Dermoscopy of a skin lesion.
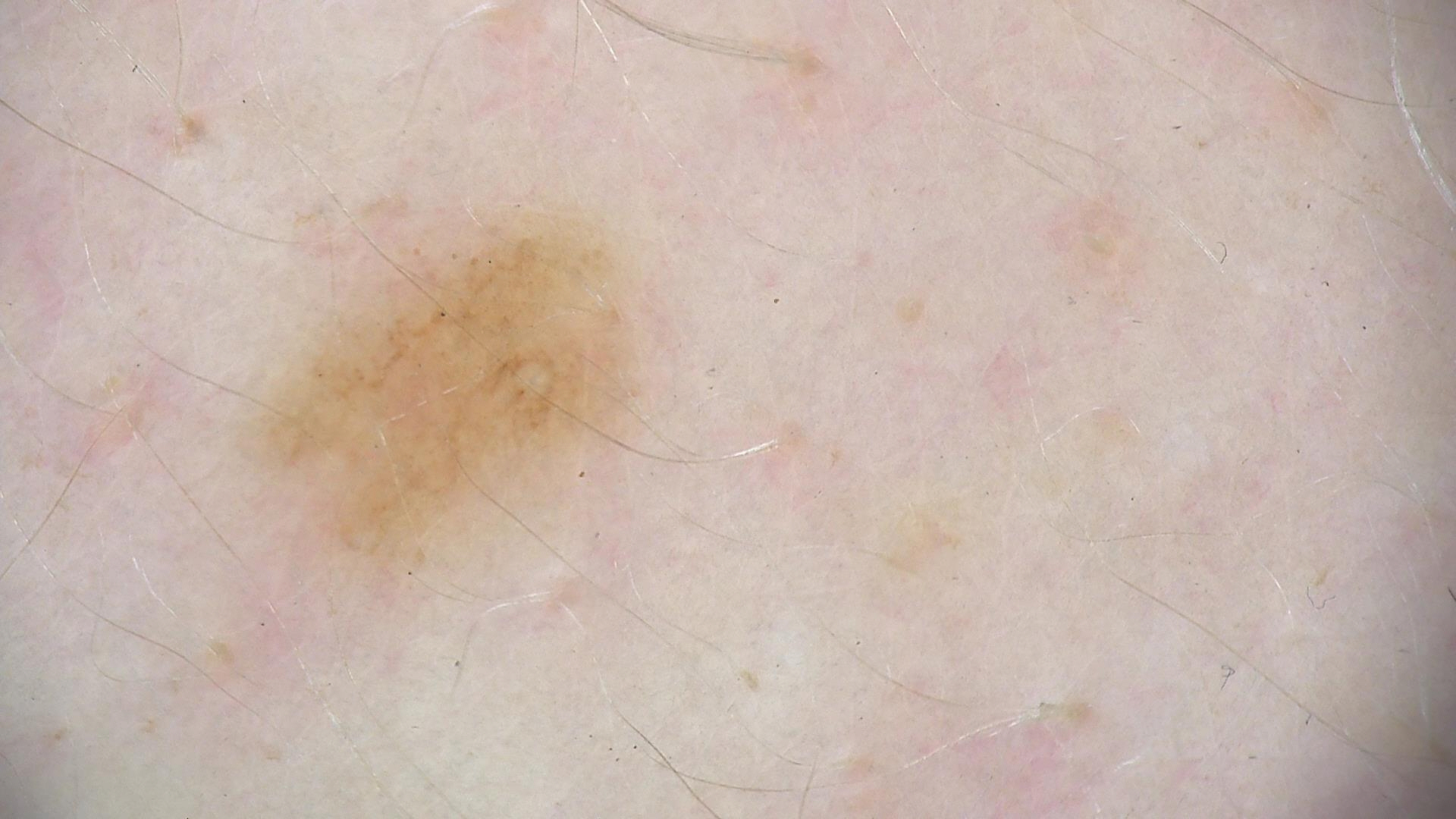Consistent with a dysplastic junctional nevus.